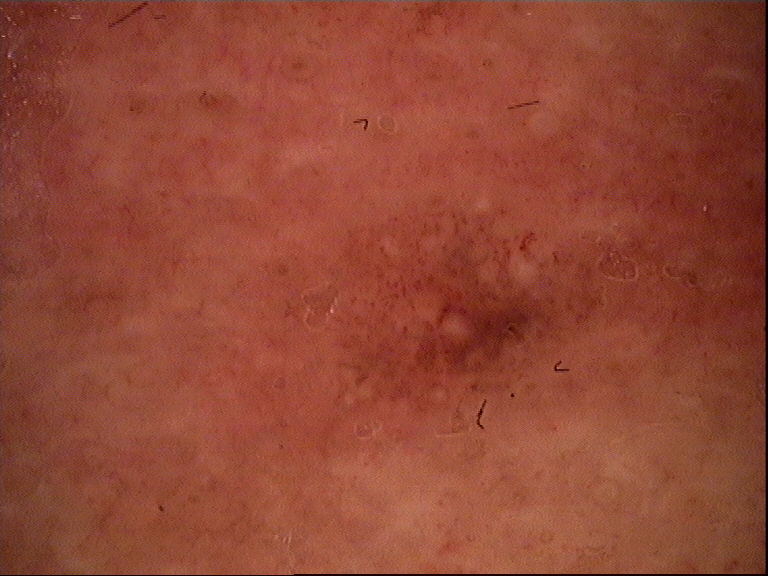<lesion>
  <diagnosis>
    <name>compound nevus</name>
    <code>cb</code>
    <malignancy>benign</malignancy>
    <super_class>melanocytic</super_class>
    <confirmation>expert consensus</confirmation>
  </diagnosis>
</lesion>